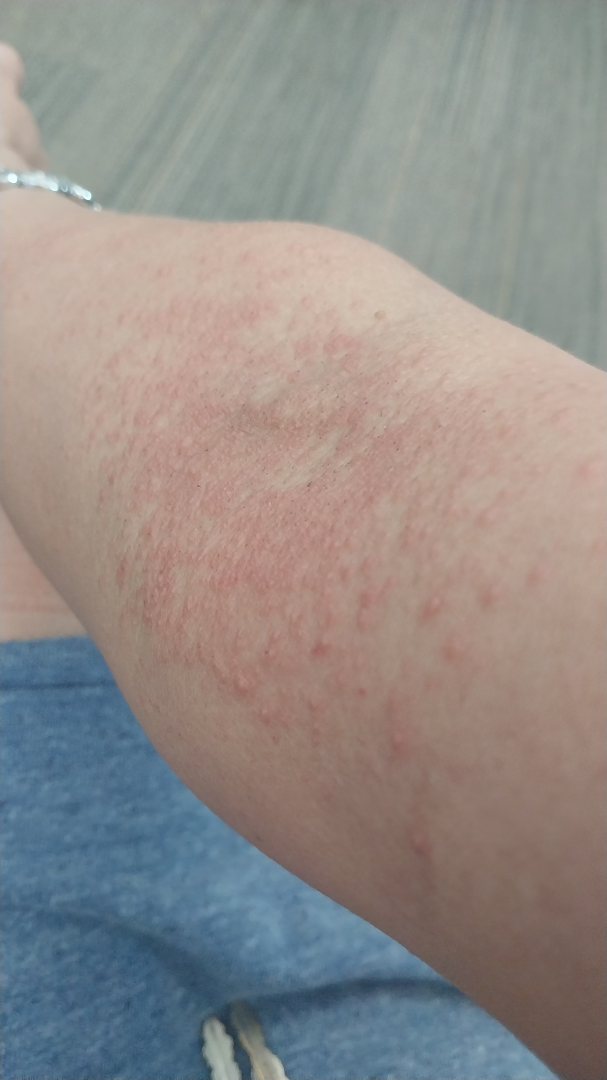The lesion is associated with bothersome appearance, itching, burning, enlargement and darkening.
The patient considered this a rash.
This image was taken at an angle.
Reported duration is less than one week.
The patient is female.
The affected area is the arm.
The lesion is described as raised or bumpy and rough or flaky.
Contact dermatitis and Eczema were considered with similar weight; with consideration of Dermatitis herpetiformis.